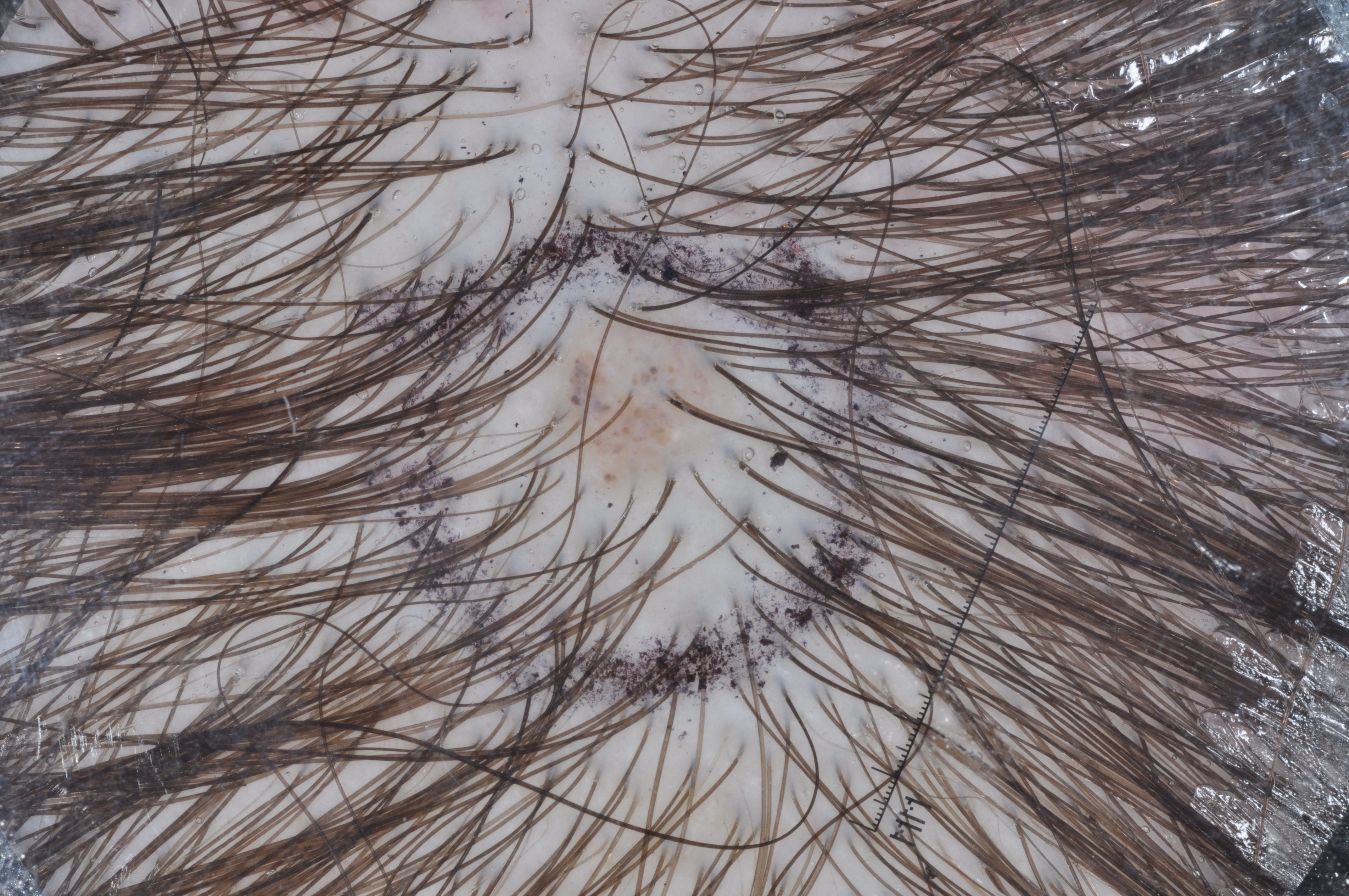<lesion>
<patient>
  <sex>female</sex>
  <age_approx>45</age_approx>
</patient>
<image>
  <modality>dermoscopy</modality>
</image>
<lesion_location>
  <bbox_xyxy>541, 294, 748, 504</bbox_xyxy>
</lesion_location>
<dermoscopic_features>
  <present/>
  <absent>milia-like cysts, pigment network, negative network, streaks</absent>
</dermoscopic_features>
<lesion_extent>small</lesion_extent>
<diagnosis>
  <name>melanocytic nevus</name>
  <malignancy>benign</malignancy>
  <lineage>melanocytic</lineage>
  <provenance>clinical</provenance>
</diagnosis>
</lesion>